A female patient age 59. The patient says their skin reddens with sun exposure. A moderate number of moles by the patient's own estimate. A clinical close-up of a skin lesion. Referred for assessment of suspected melanocytic nevus:
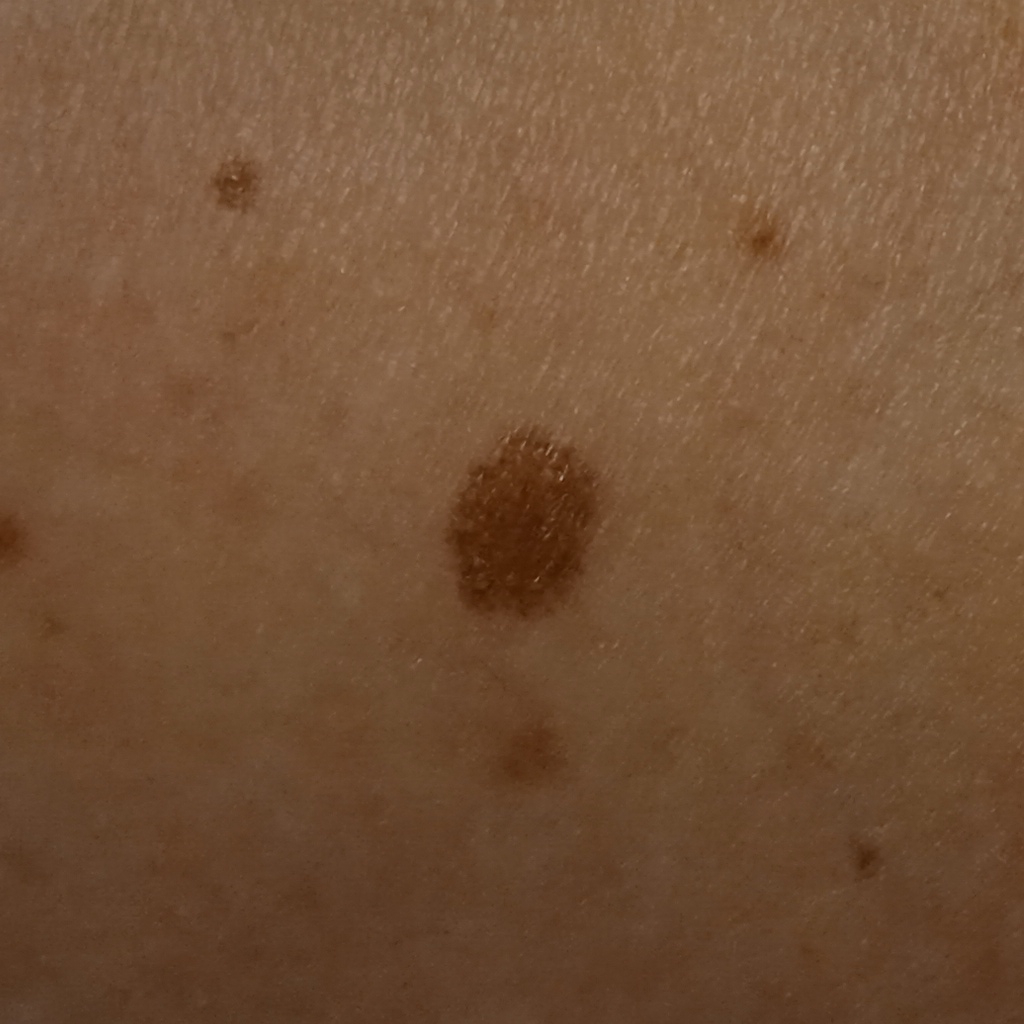{"lesion_location": "an arm", "lesion_size": {"diameter_mm": 6.7}, "diagnosis": {"name": "atypical (dysplastic) nevus", "malignancy": "benign", "procedure": "excision"}}